The patient is male; a close-up photograph; the lesion involves the leg, back of the hand and arm:
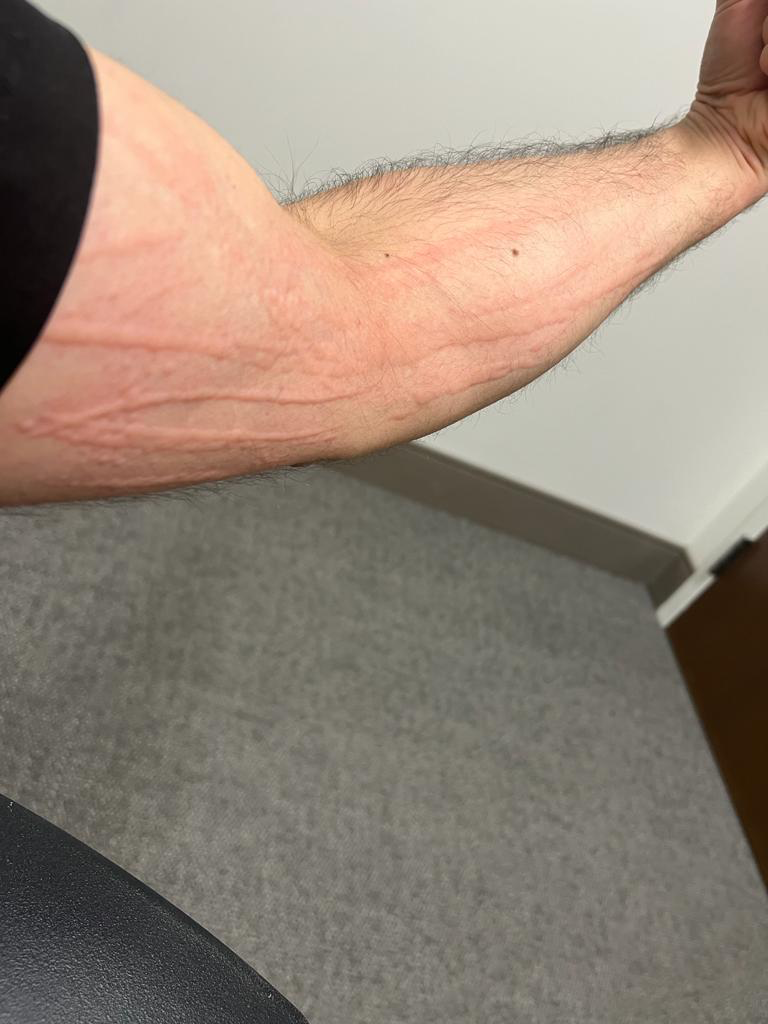Q: What is the differential diagnosis?
A: the impression is Urticaria